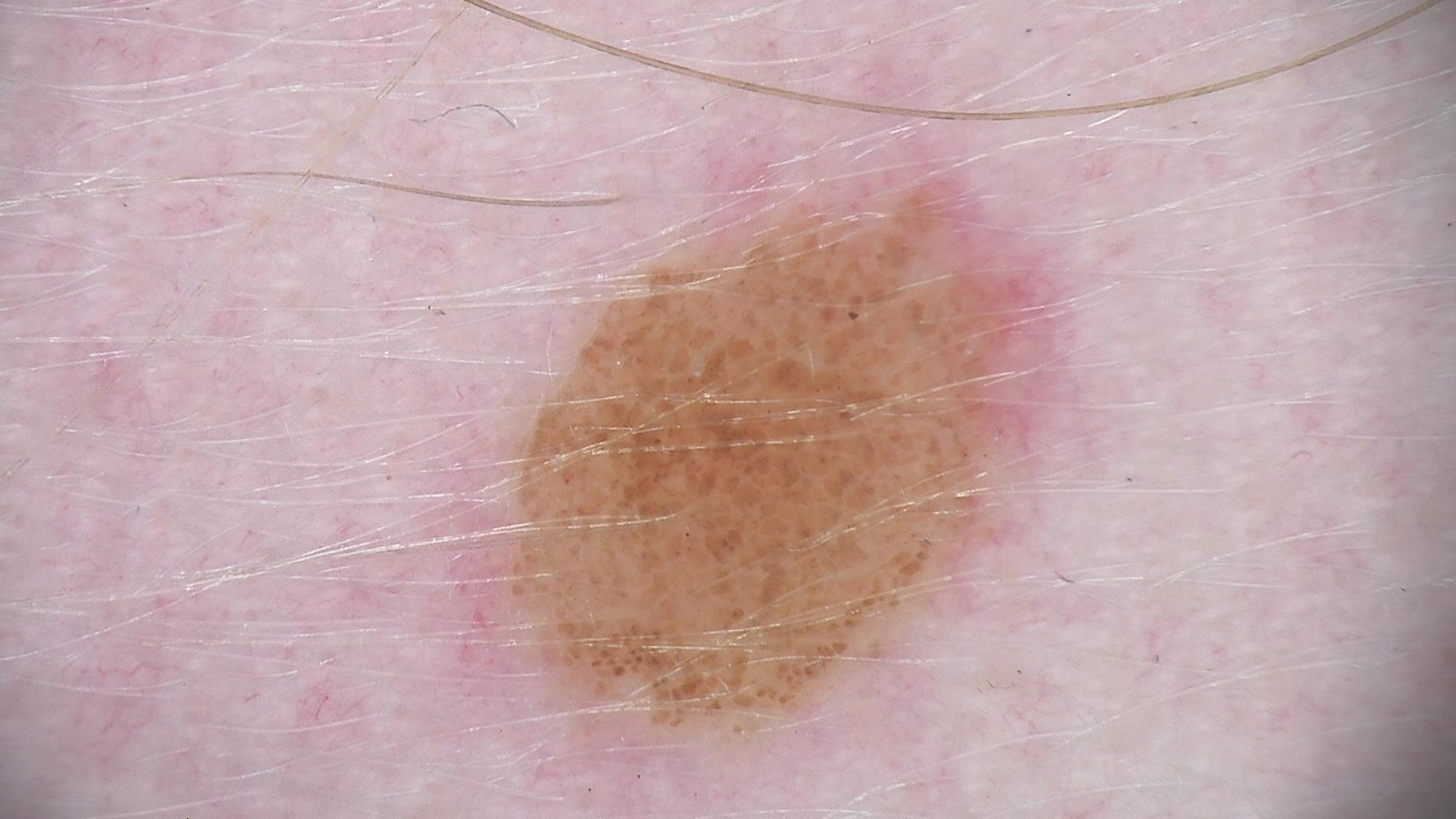Findings:
• assessment — compound nevus (expert consensus)